The affected area is the arm · the patient is 40–49, male · this image was taken at an angle — 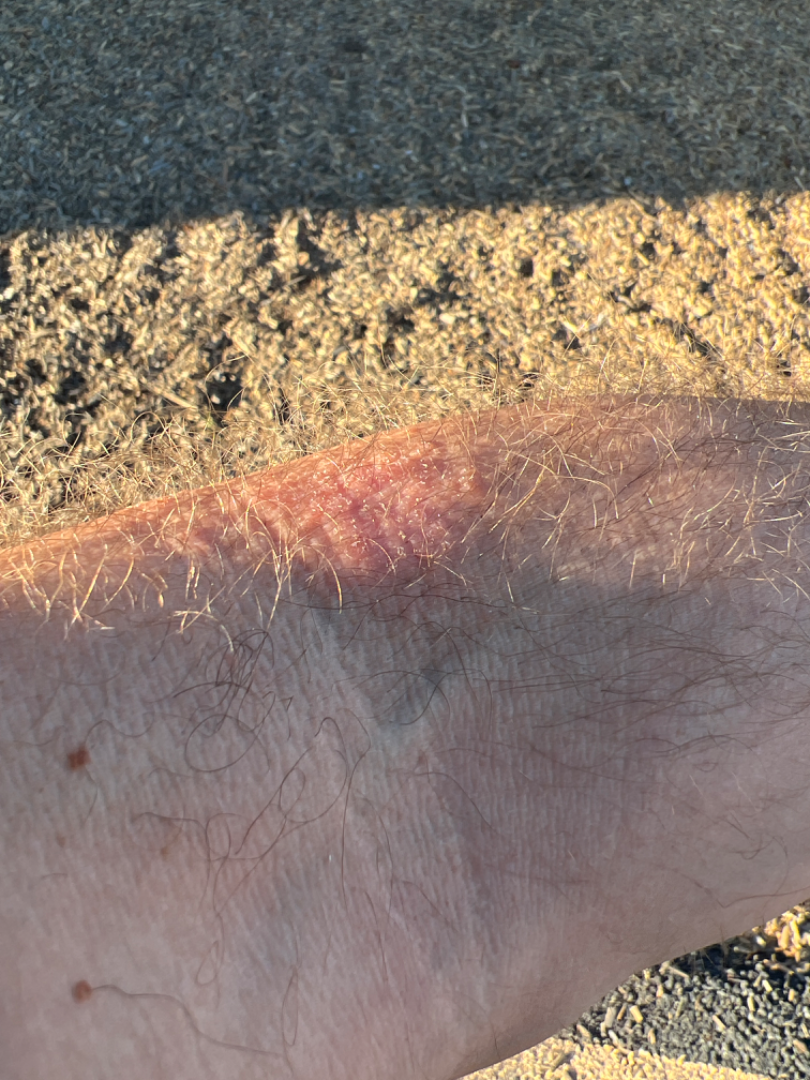Reported duration is less than one week.
The contributor reports the lesion is raised or bumpy.
The patient also reports shortness of breath.
Allergic Contact Dermatitis (most likely).